The chart notes prior skin cancer (patient or family); a female patient 53 years of age: 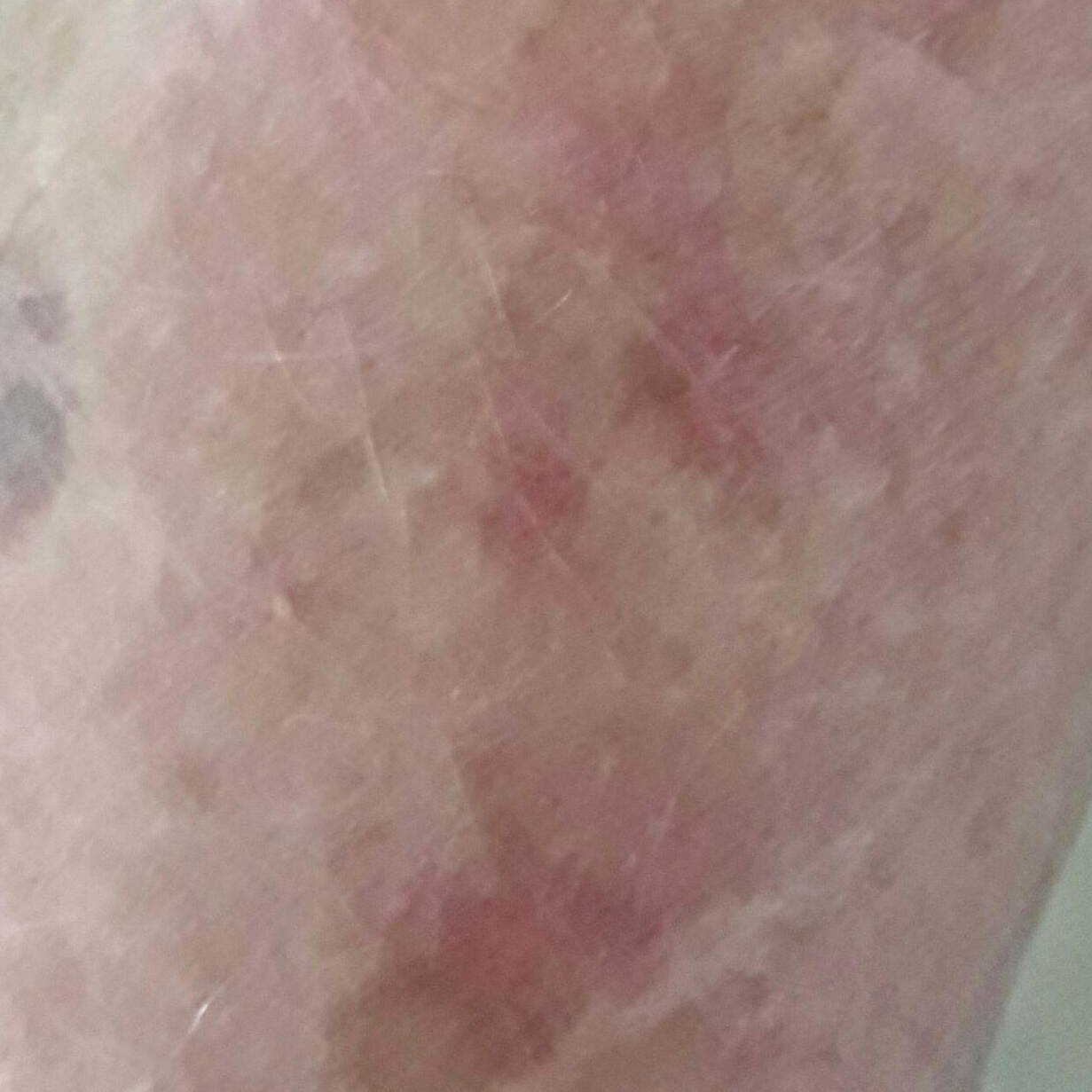site: a forearm; lesion diameter: approx. 9 × 7 mm; assessment: actinic keratosis (clinical consensus).